Skin tone: Fitzpatrick skin type II; human graders estimated a Monk Skin Tone of 2. This image was taken at a distance: 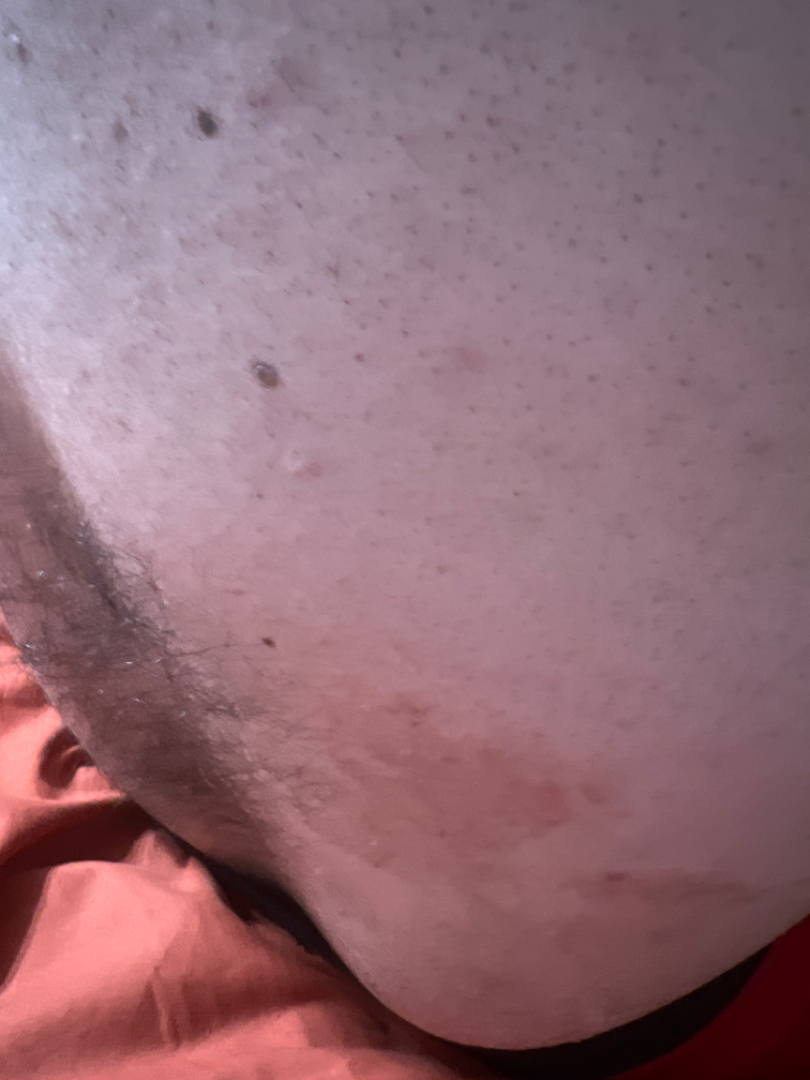On teledermatology review: the leading consideration is Tinea; also consider Psoriasis; also raised was Eczema.